A dermoscopy image of a single skin lesion:
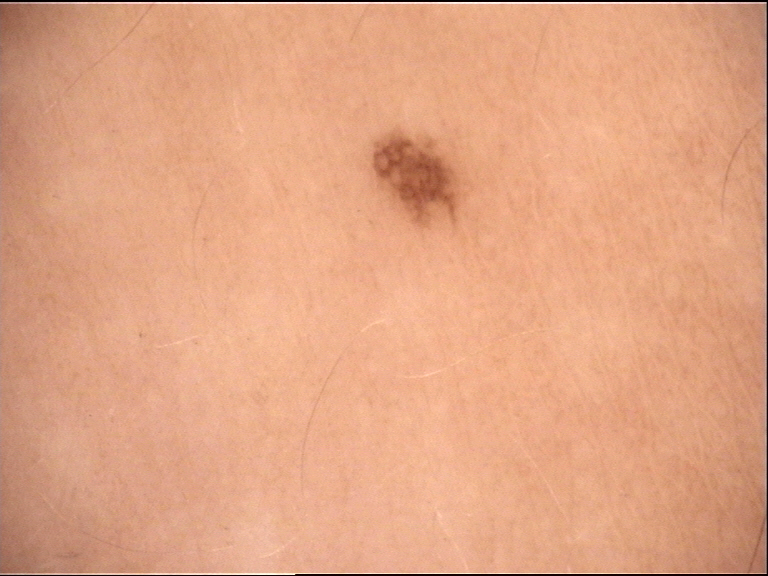Q: How is the lesion classified?
A: banal
Q: What is the diagnosis?
A: junctional nevus (expert consensus)